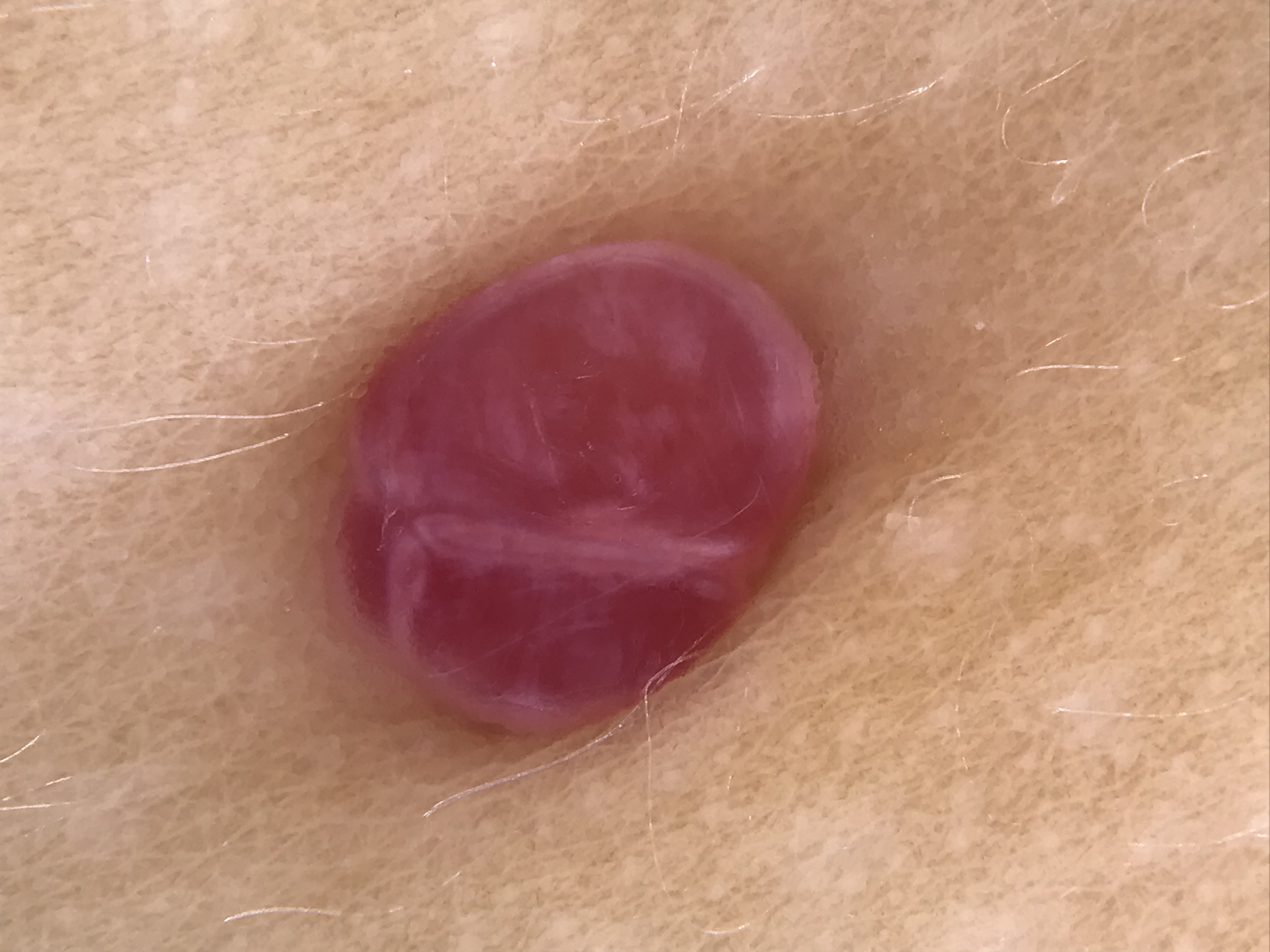<dermoscopy>
<diagnosis>
<name>pyogenic granuloma</name>
<code>pg</code>
<malignancy>benign</malignancy>
<super_class>non-melanocytic</super_class>
<confirmation>expert consensus</confirmation>
</diagnosis>
</dermoscopy>